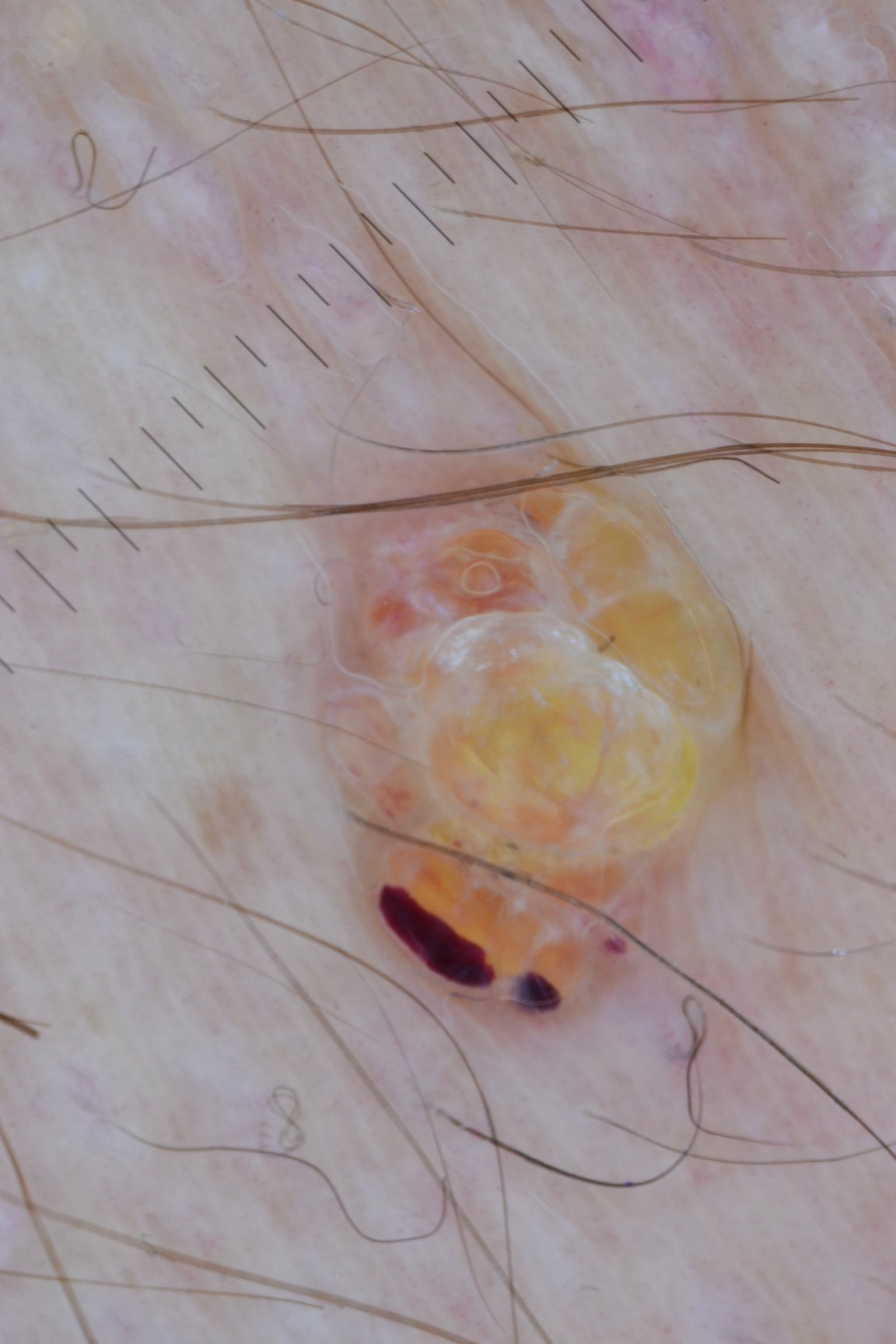Findings:
– image type — dermatoscopy
– label — lymphangioma (expert consensus)